A dermoscopic image of a skin lesion; a male patient approximately 30 years of age.
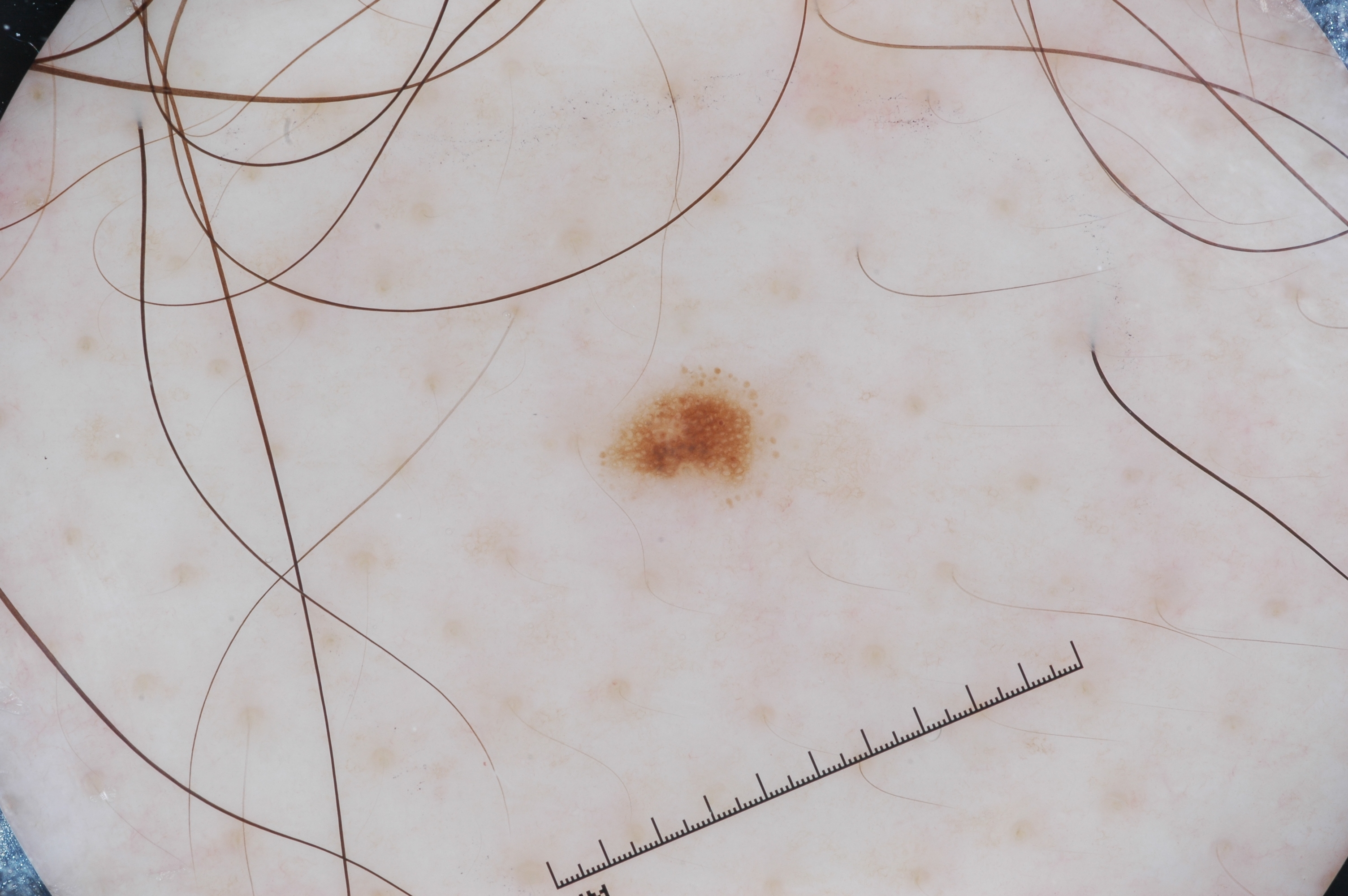lesion extent — ~1% of the field | location — [611,378,758,483] | dermoscopic findings — pigment network | diagnosis — a melanocytic nevus, a benign lesion.